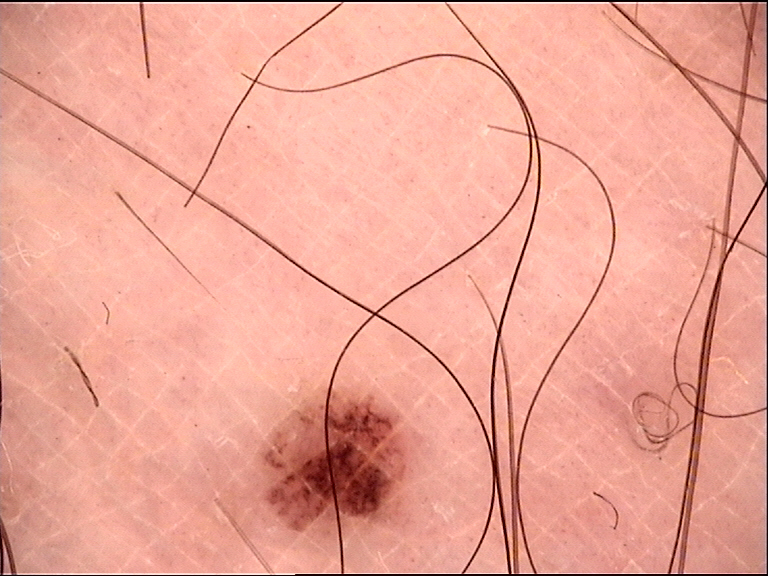Conclusion: Diagnosed as a dysplastic junctional nevus.